A skin lesion imaged with a dermatoscope.
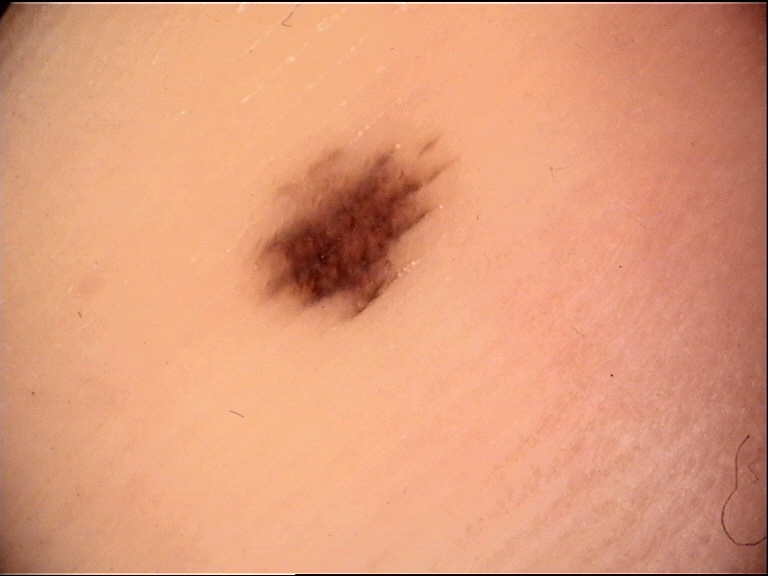{"lesion_type": {"main_class": "banal", "pattern": "junctional"}, "diagnosis": {"name": "acral junctional nevus", "code": "ajb", "malignancy": "benign", "super_class": "melanocytic", "confirmation": "expert consensus"}}